A female patient 73 years of age; history notes tobacco use and no prior skin cancer (patient or family); recorded as Fitzpatrick skin type II; a clinical close-up photograph of a skin lesion: 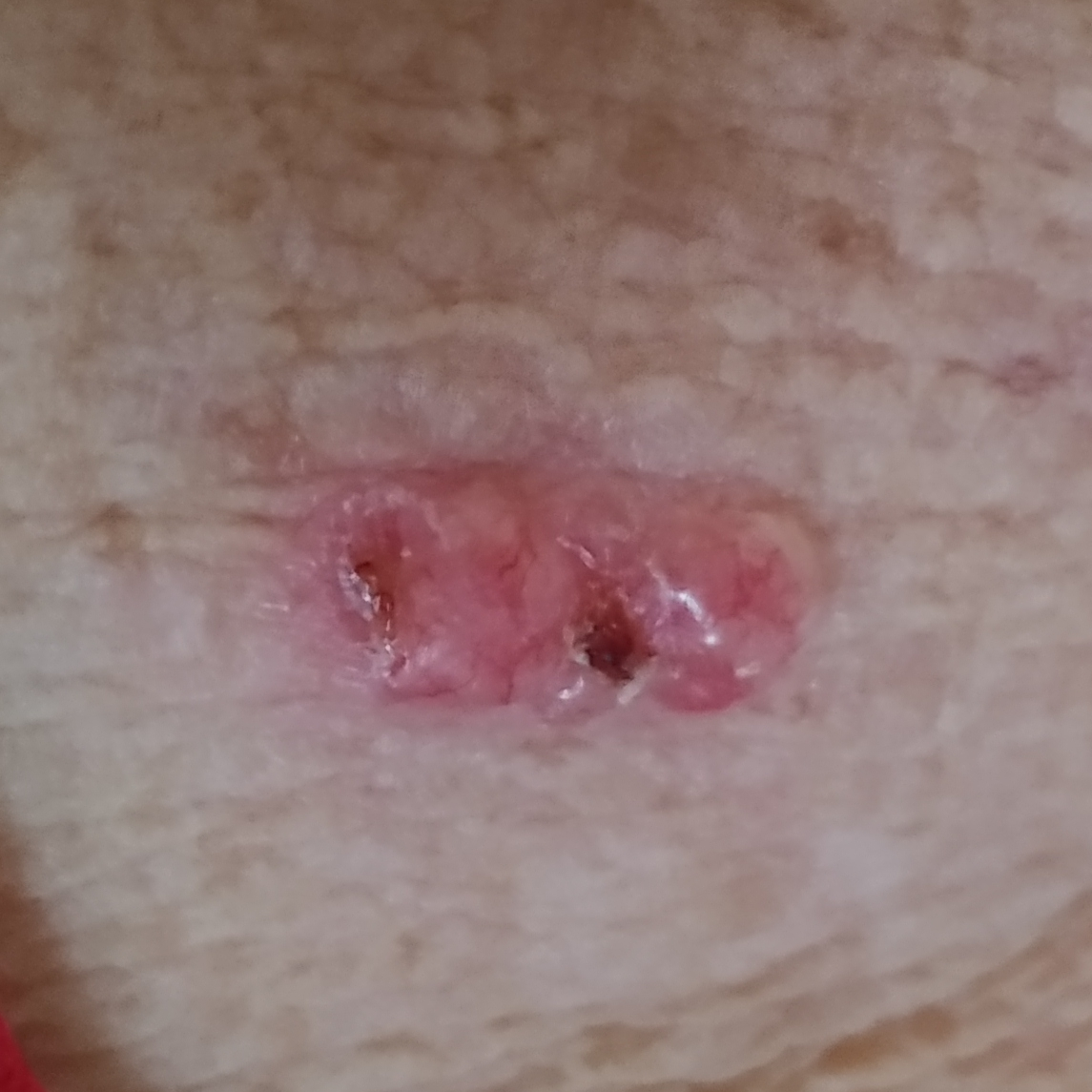Q: What is the anatomic site?
A: an arm
Q: Lesion size?
A: approx. 18 × 8 mm
Q: What symptoms does the patient report?
A: itching, elevation, growth, change in appearance, bleeding
Q: What did the workup show?
A: basal cell carcinoma (biopsy-proven)